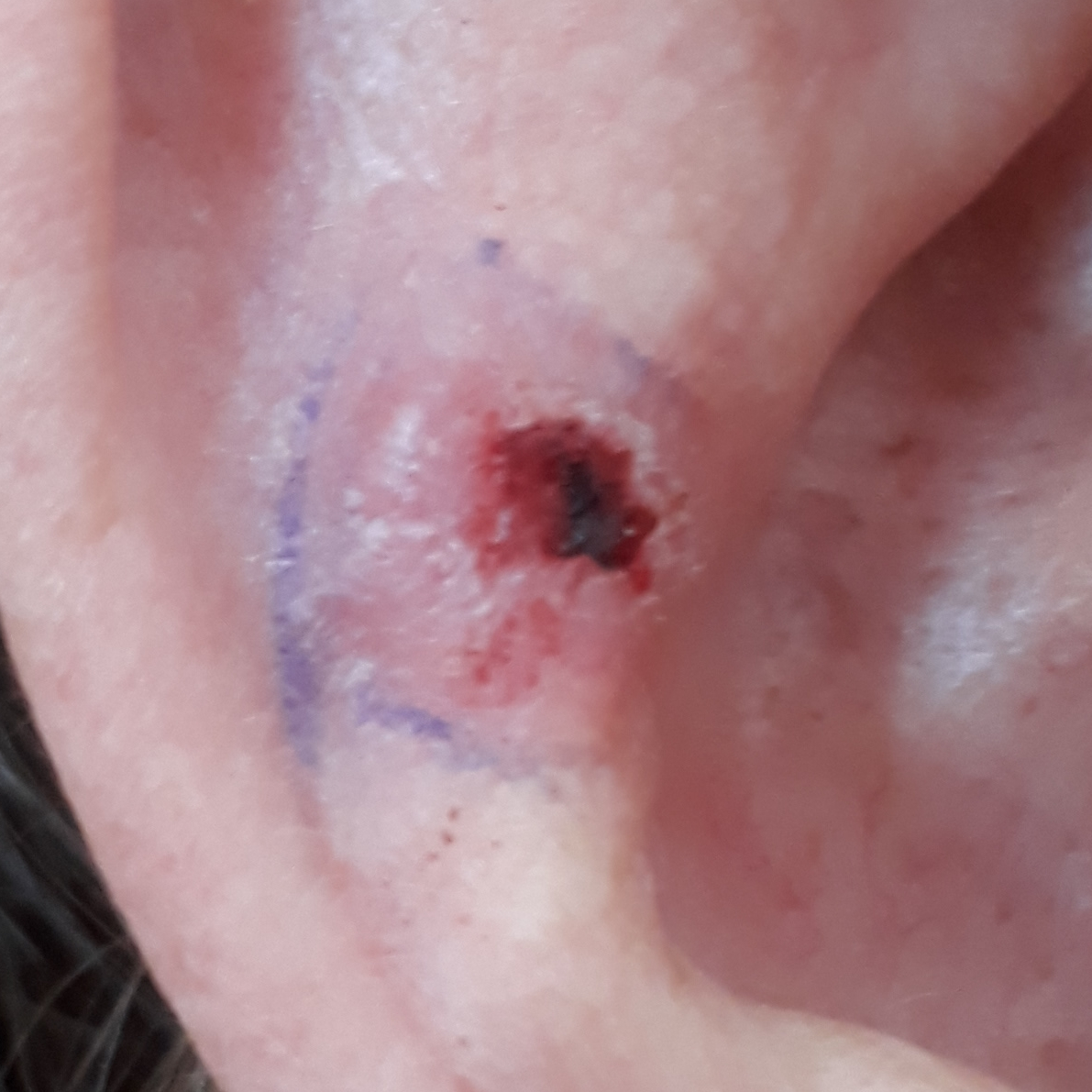A clinical photograph of a skin lesion. The lesion is on an ear. The patient reports that the lesion has bled, is elevated, and itches. On biopsy, the diagnosis was a basal cell carcinoma.